A female subject 59 years of age — 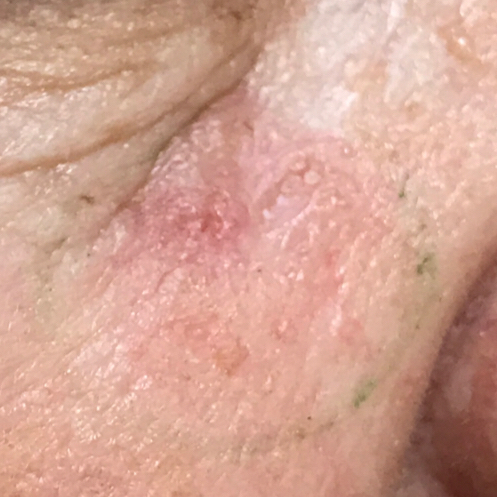The lesion is located on the face.
The patient describes that the lesion itches, but is not elevated and has not bled.
Histopathologically confirmed as a basal cell carcinoma.